A female patient aged 18 to 22 · a dermoscopic close-up of a skin lesion — 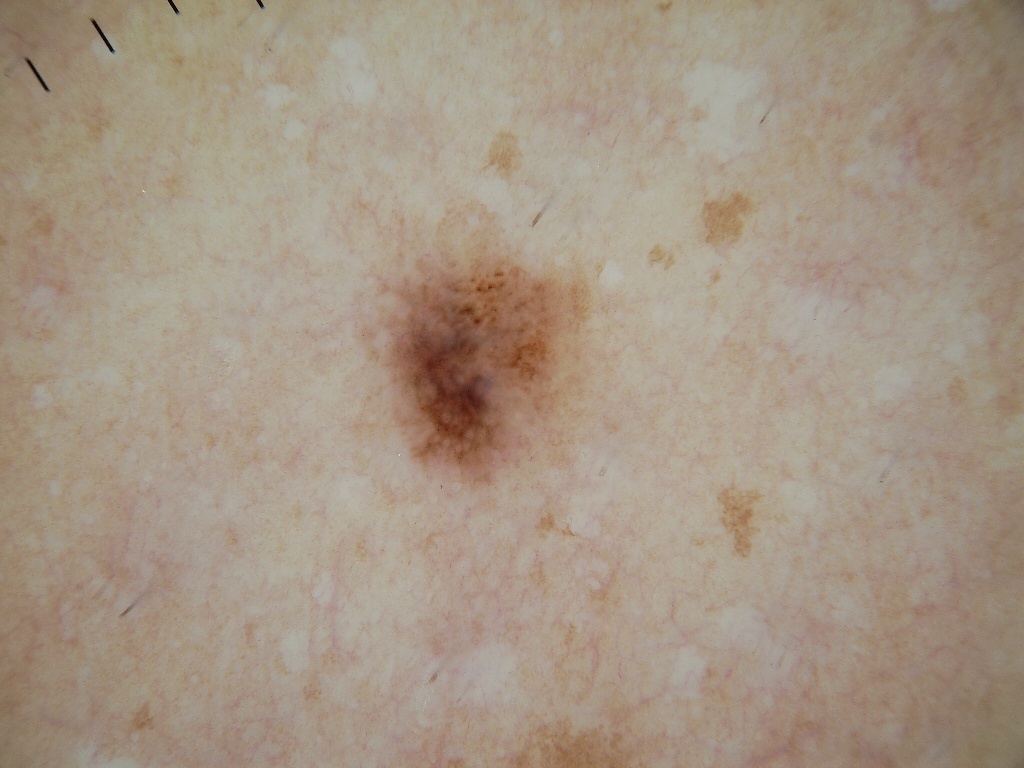location: 340/218/599/499
features: pigment network
assessment: a melanocytic nevus